The leg is involved, present for one to four weeks, a close-up photograph:
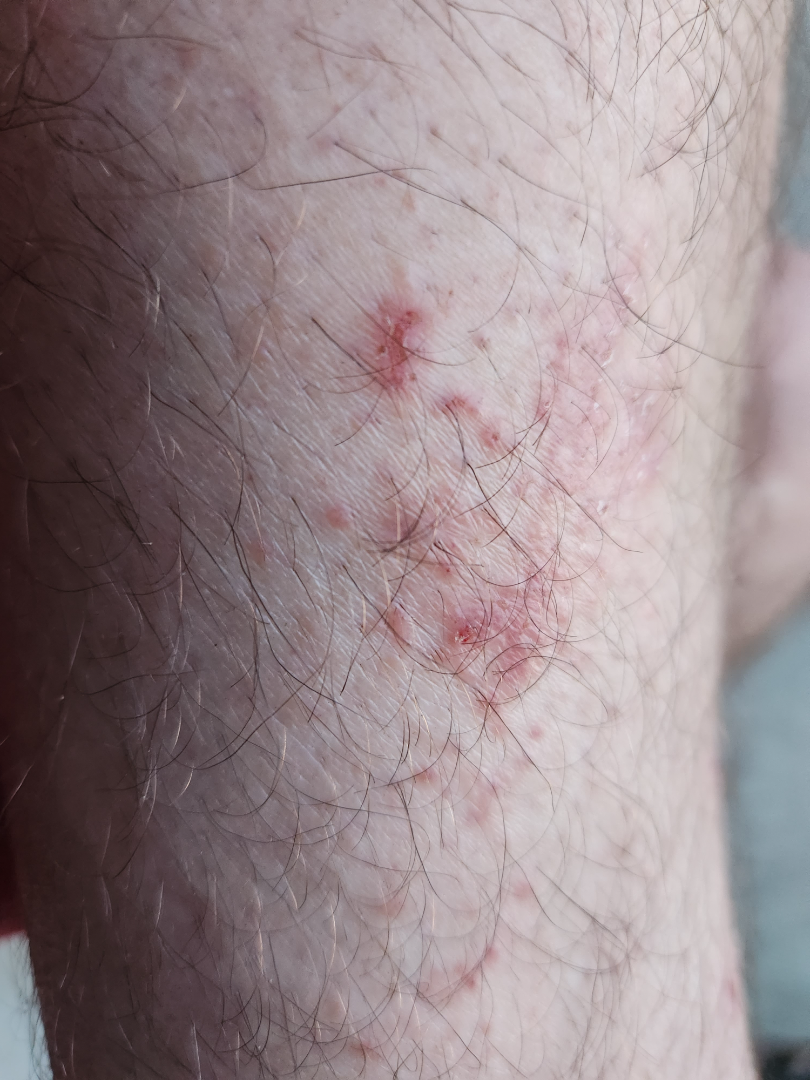{"assessment": "indeterminate from the photograph"}